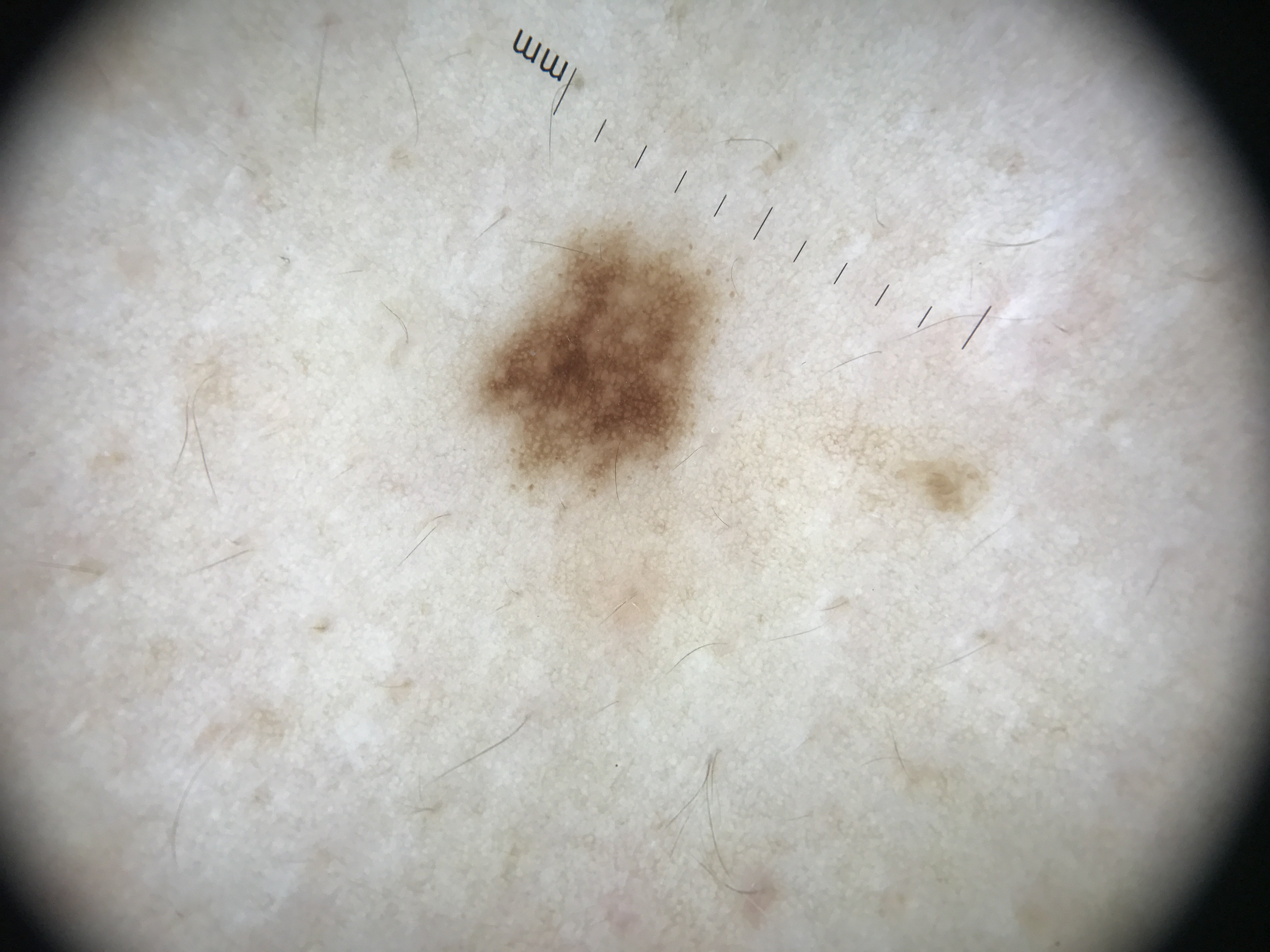Findings:
A dermoscopic photograph of a skin lesion.
Conclusion:
The diagnosis was a dysplastic junctional nevus.